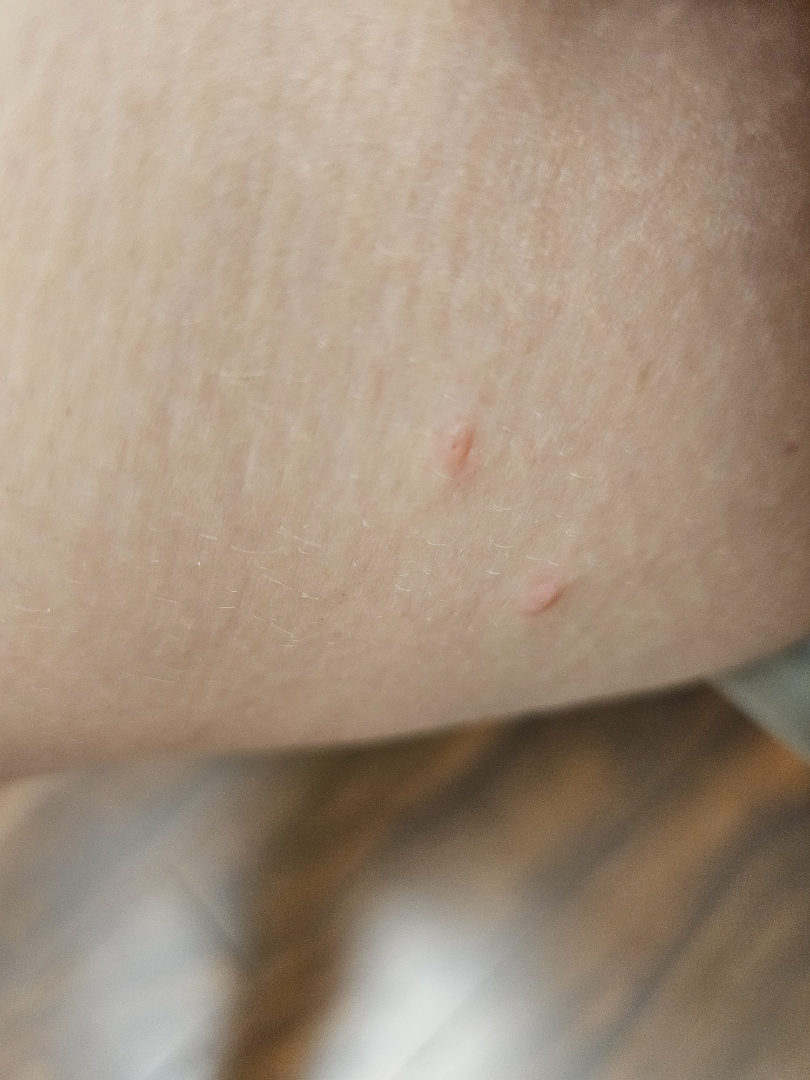view = at an angle
contributor = female, age 30–39
site = front of the torso, back of the torso, head or neck and arm
impression = the leading consideration is Insect Bite; also raised was Eczema; an alternative is Urticaria